The condition has been present for less than one week. Fitzpatrick II; human graders estimated Monk skin tone scale 3 (US pool) or 2 (India pool). Reported lesion symptoms include pain, enlargement, bothersome appearance, burning, darkening, bleeding and itching. Self-categorized by the patient as a rash. The contributor reports associated joint pain. The arm is involved. This image was taken at a distance. The lesion is described as raised or bumpy, fluid-filled and rough or flaky: 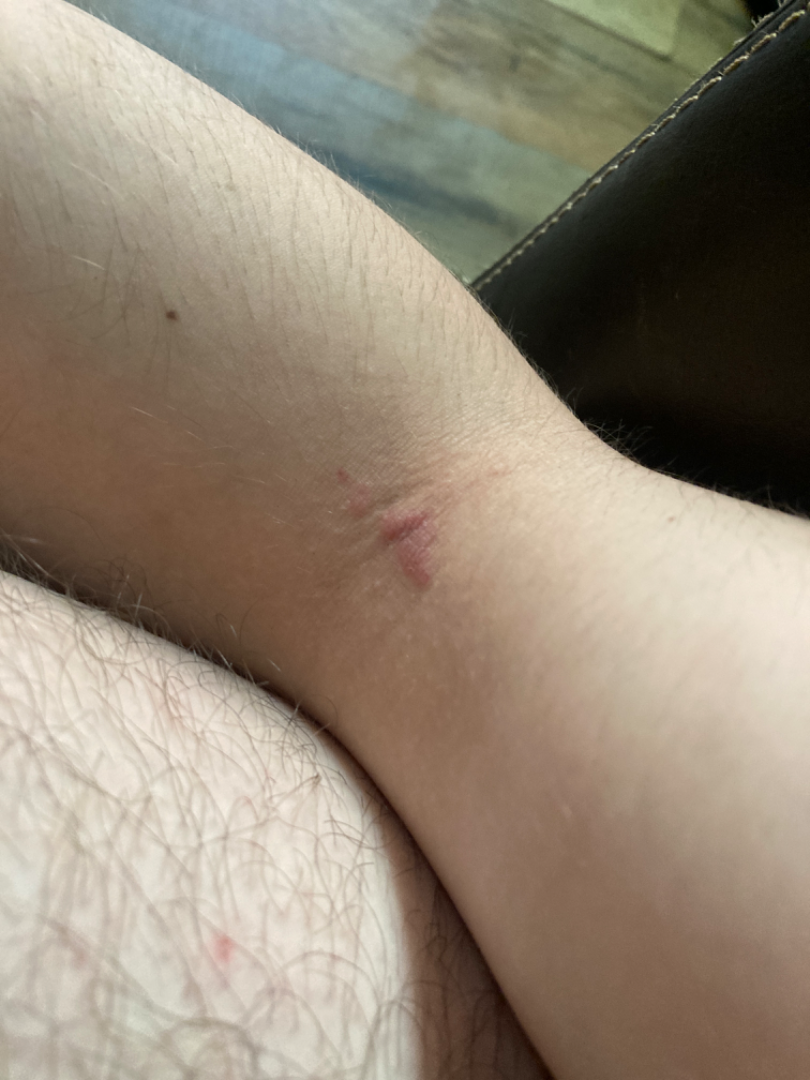On remote review of the image, the impression was split between pathergy and Kaposi's sarcoma of skin.